The top or side of the foot and leg are involved; an image taken at a distance.
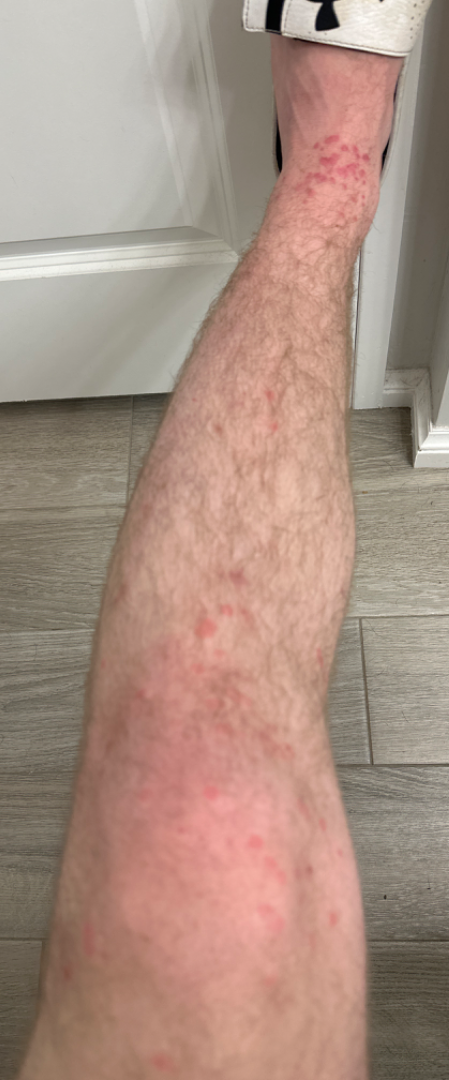The image was not sufficient for the reviewer to characterize the skin condition.